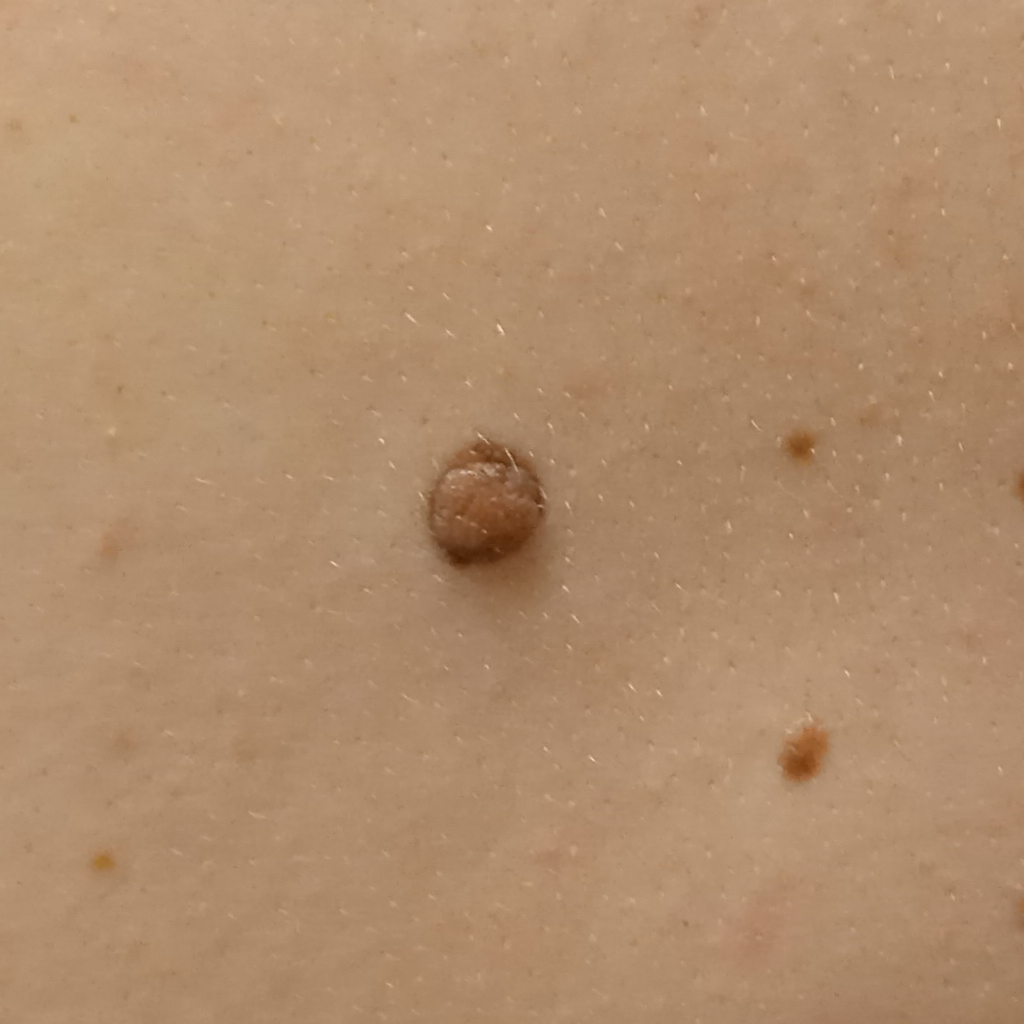Acquired for a research image collection, with no referral diagnosis. A female patient 26 years of age. Located on the back. The lesion is about 8.9 mm across. The consensus diagnosis for this lesion was a melanocytic nevus.